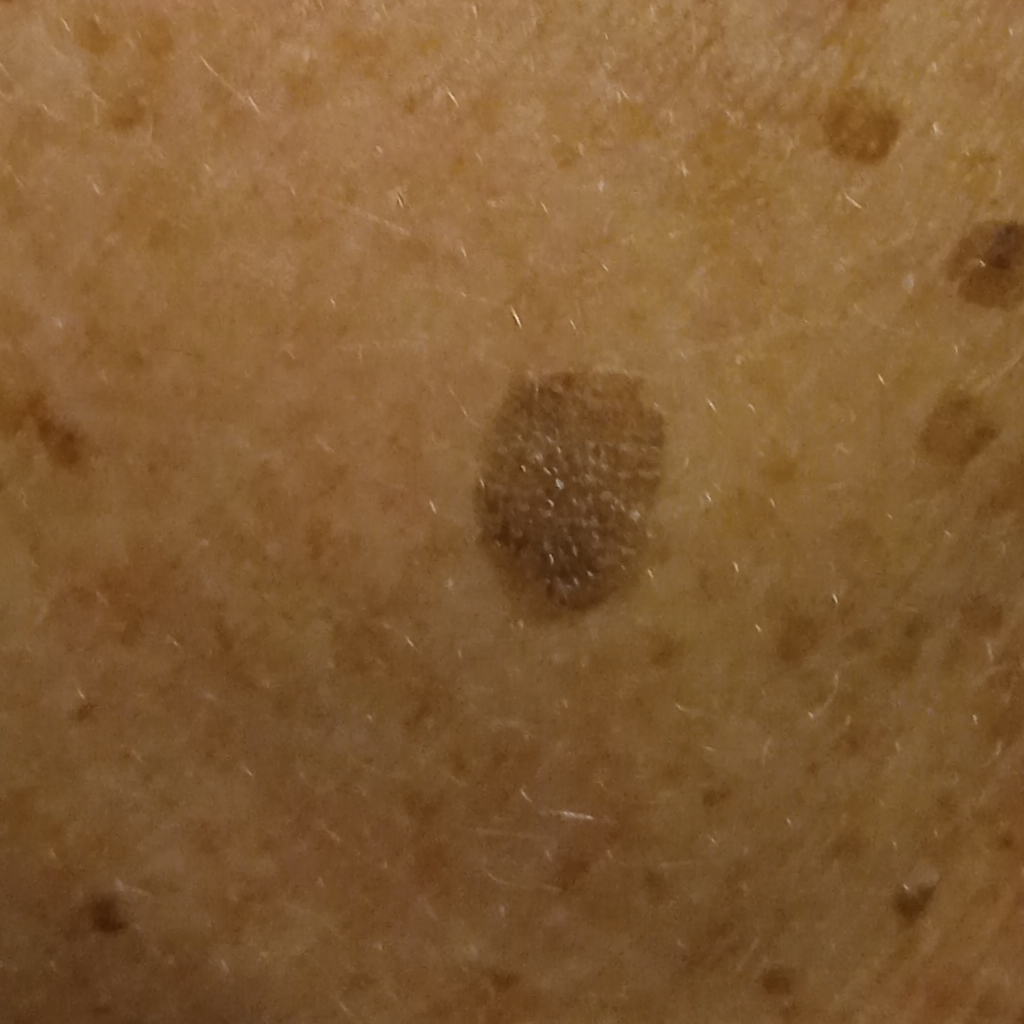Assessment:
The consensus diagnosis for this lesion was a seborrheic keratosis.